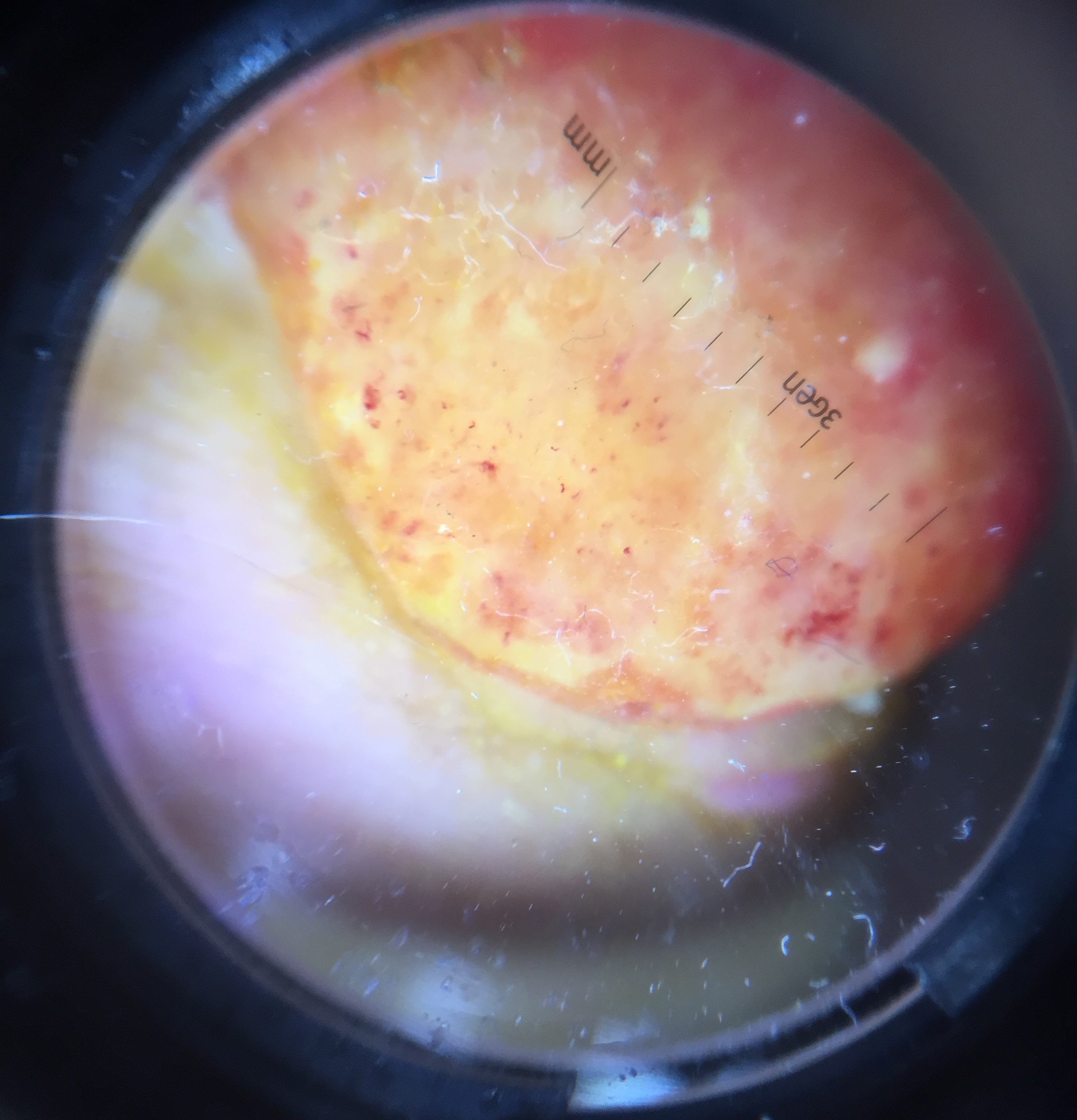Case:
A dermoscopic close-up of a skin lesion.
Conclusion:
Histopathologically confirmed as an acral nodular melanoma.